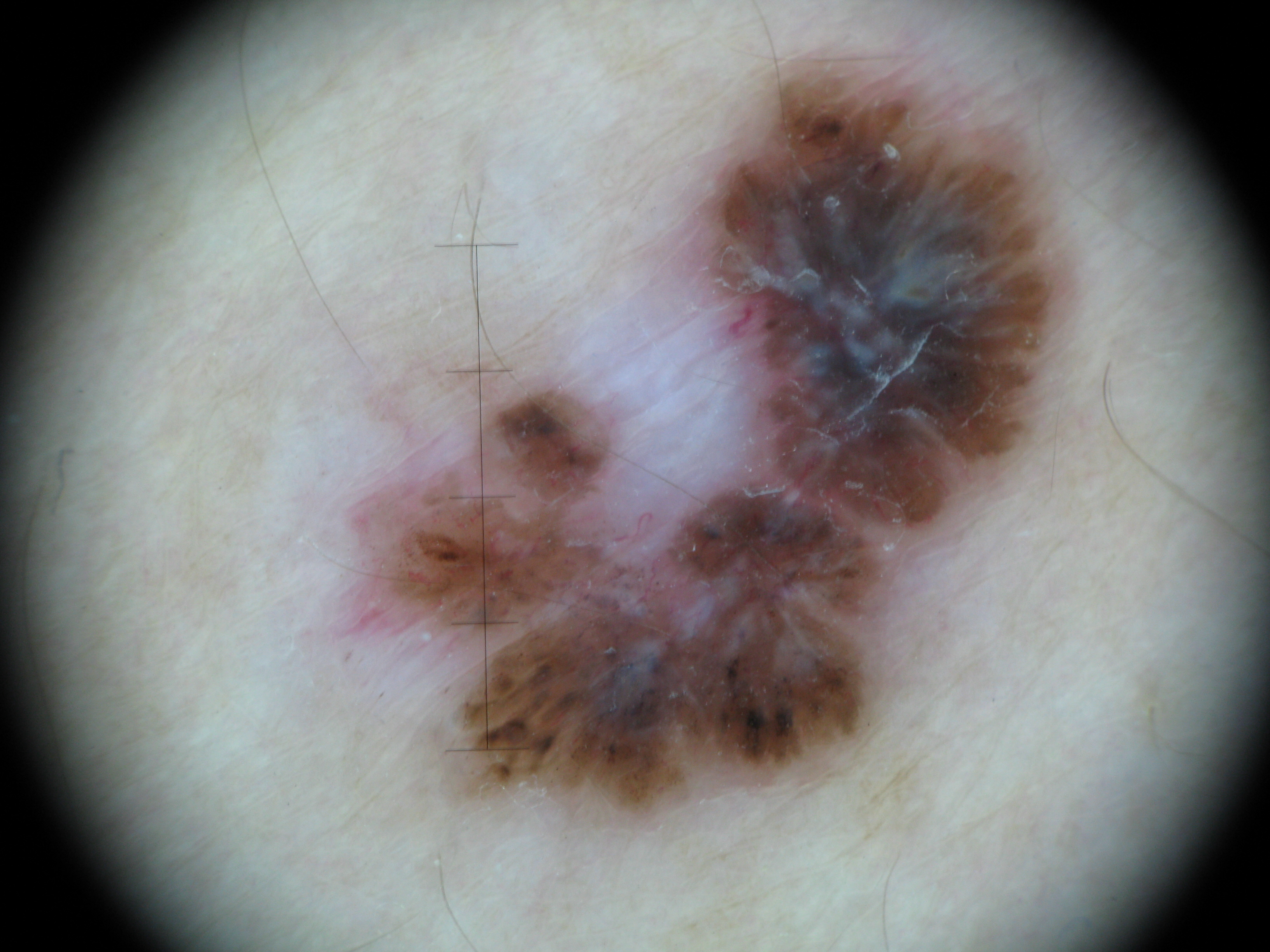Findings: A dermoscopic image of a skin lesion. Pathology: The biopsy diagnosis was a keratinocytic, malignant lesion — a basal cell carcinoma.